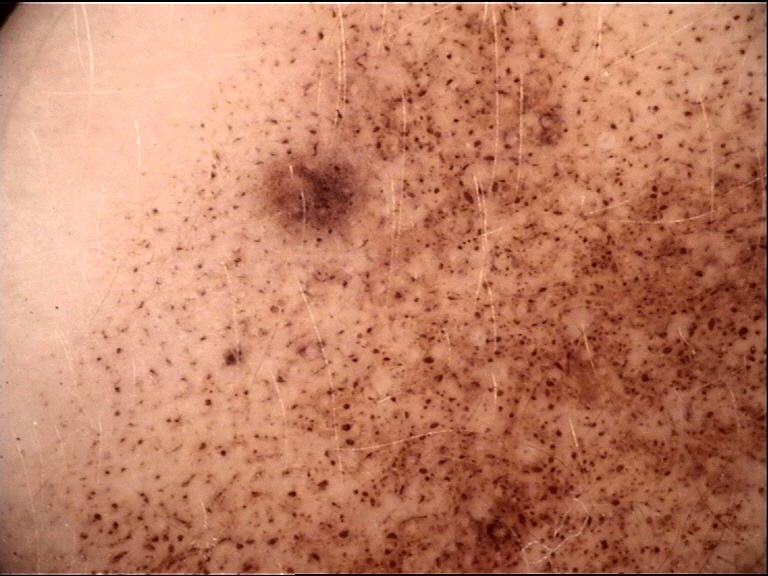label: congenital junctional nevus (expert consensus).